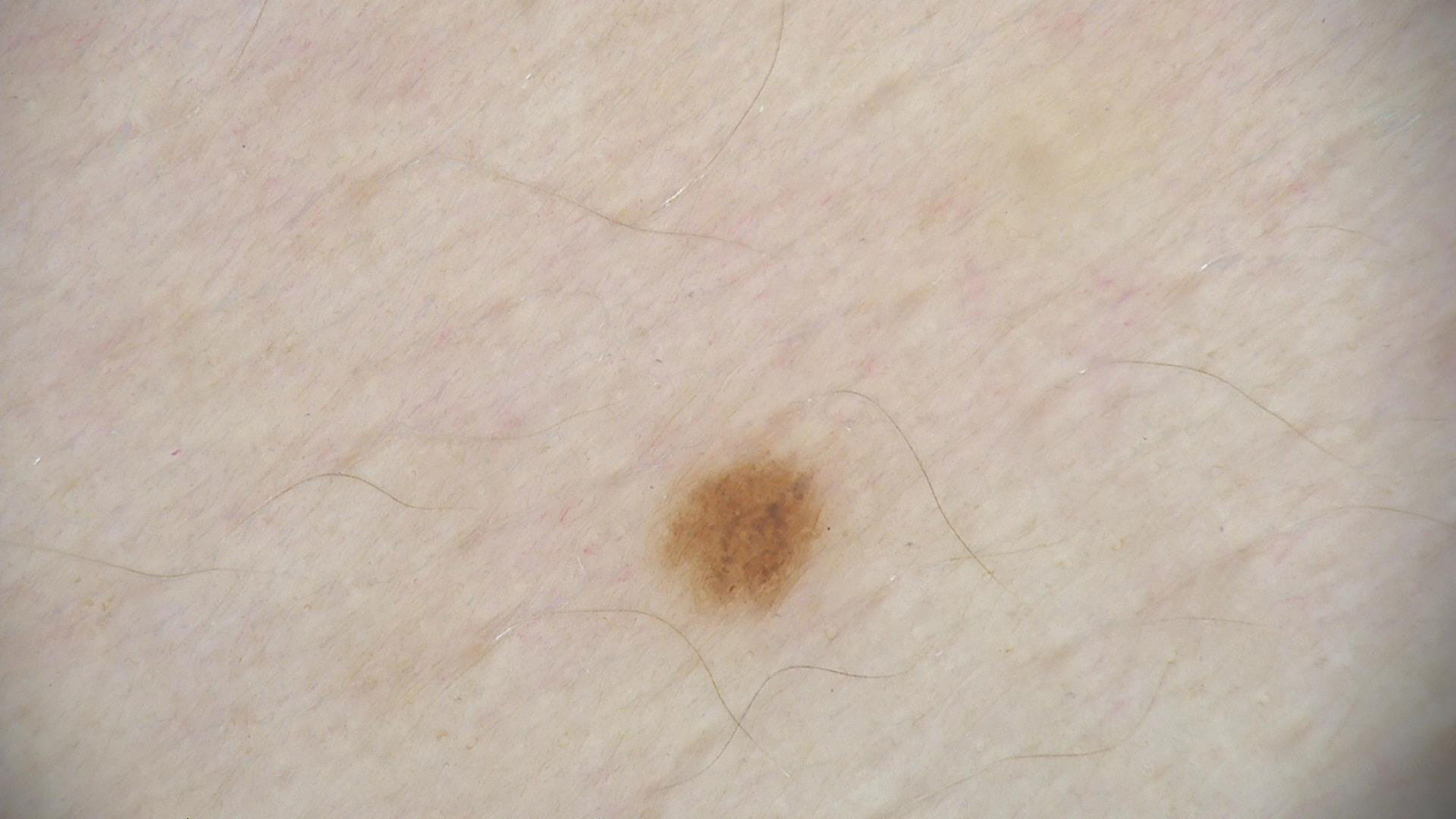{
  "image": "dermoscopy",
  "diagnosis": {
    "name": "dysplastic junctional nevus",
    "code": "jd",
    "malignancy": "benign",
    "super_class": "melanocytic",
    "confirmation": "expert consensus"
  }
}